A dermatoscopic image of a skin lesion.
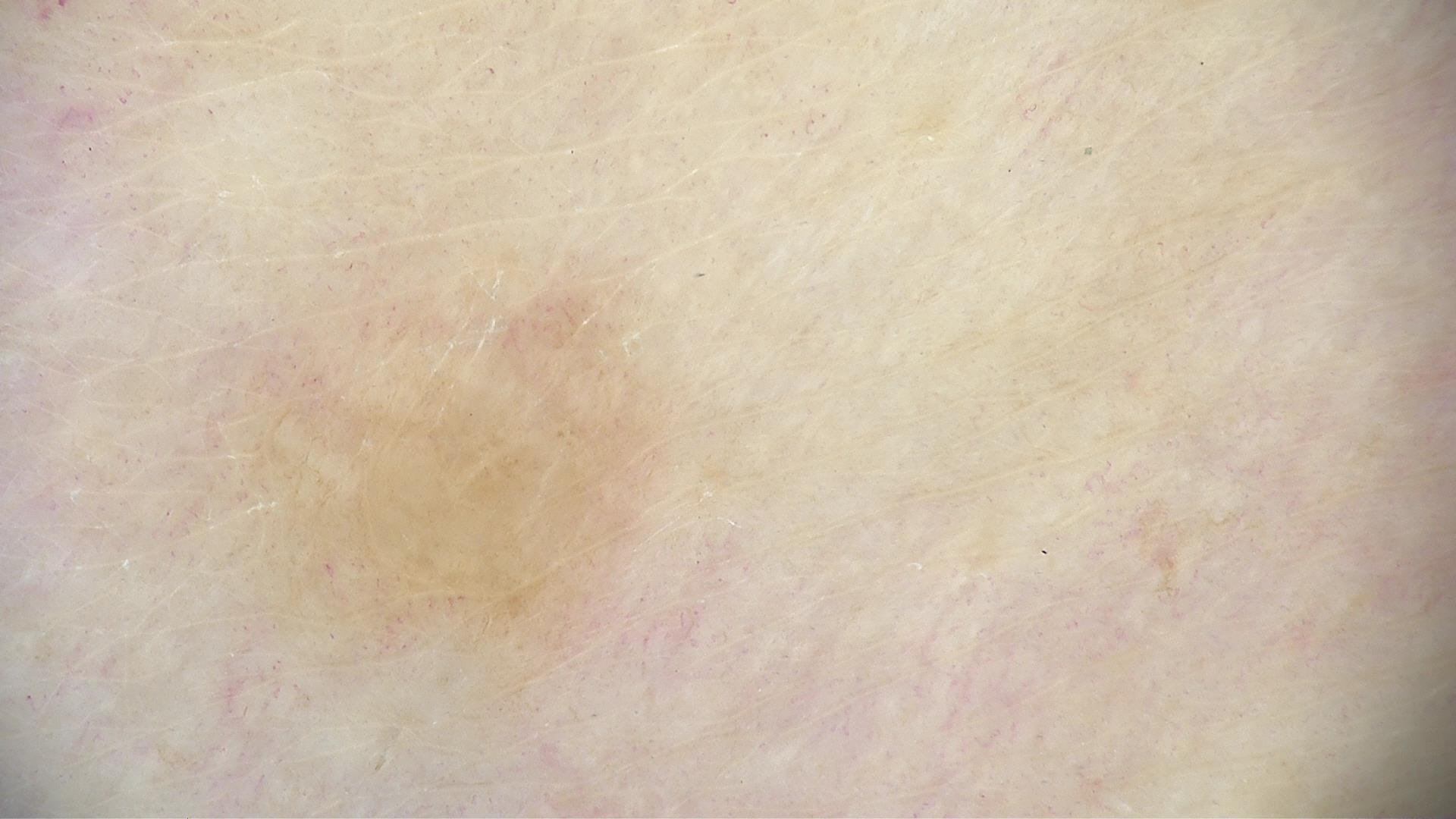The morphology is that of a banal lesion. Labeled as a junctional nevus.